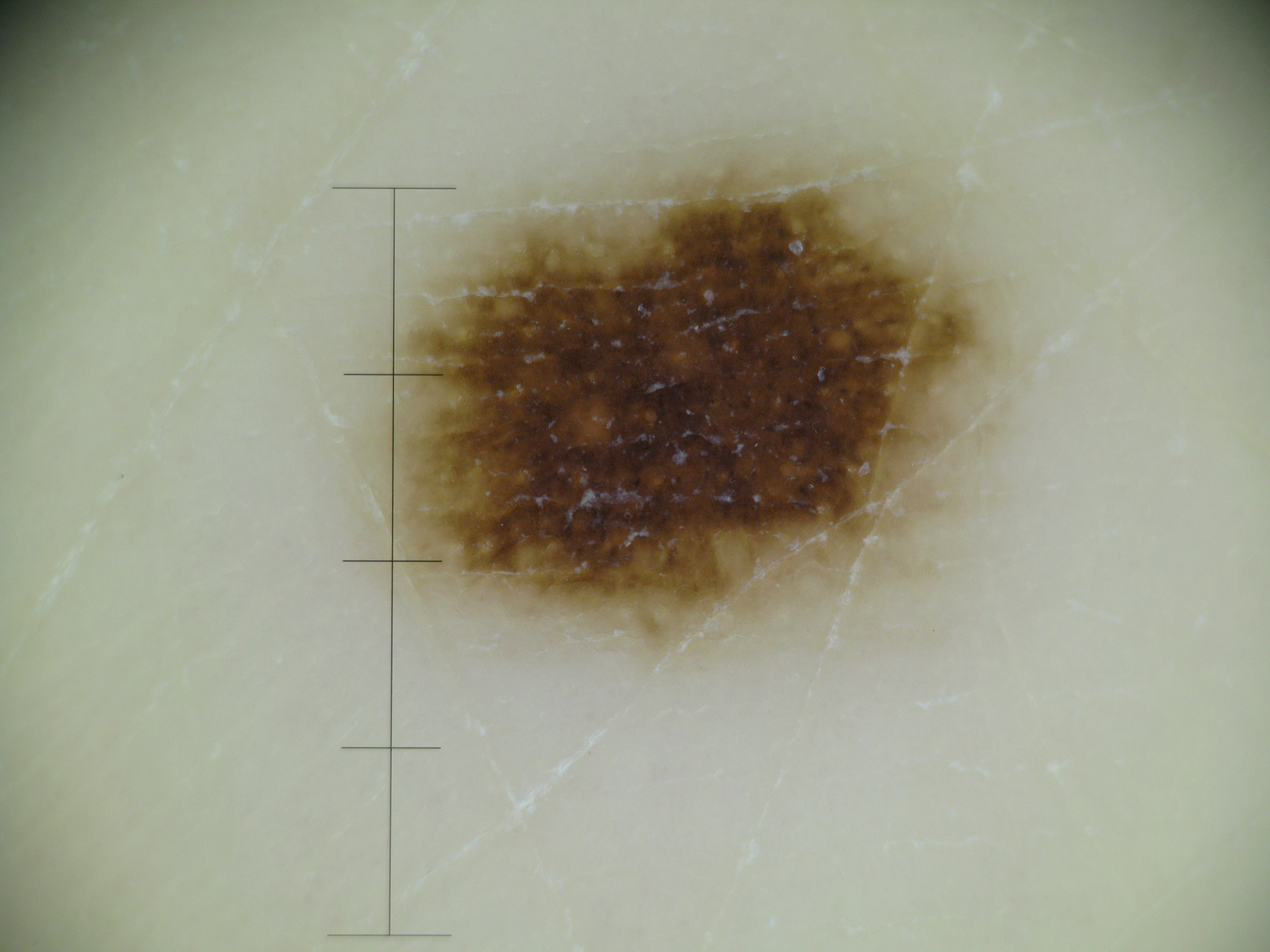A dermoscopic image of a skin lesion.
Classified as an acral dysplastic junctional nevus.